A dermoscopic close-up of a skin lesion.
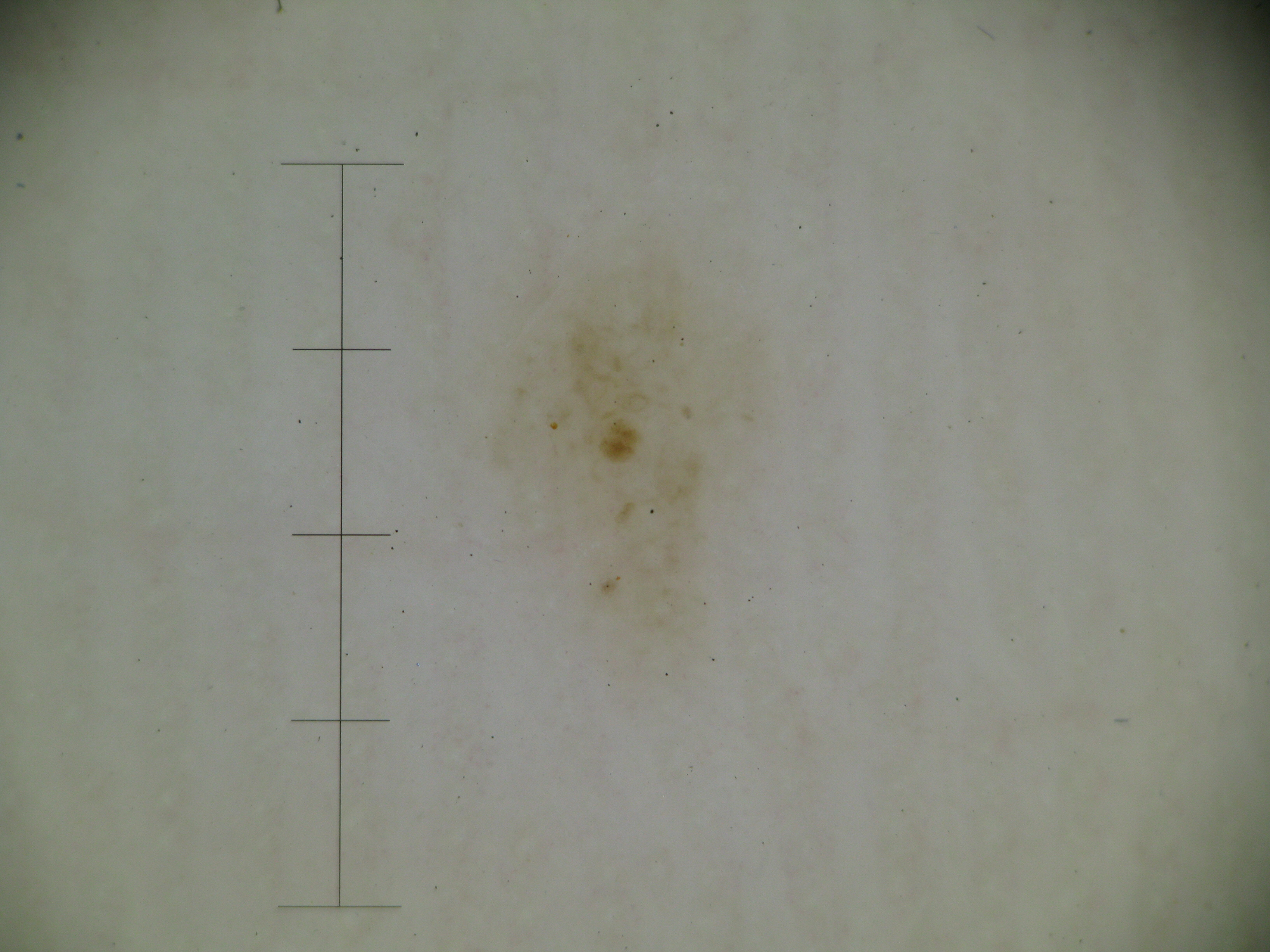{
  "lesion_type": {
    "main_class": "banal",
    "pattern": "junctional"
  },
  "diagnosis": {
    "name": "acral junctional nevus",
    "code": "ajb",
    "malignancy": "benign",
    "super_class": "melanocytic",
    "confirmation": "expert consensus"
  }
}